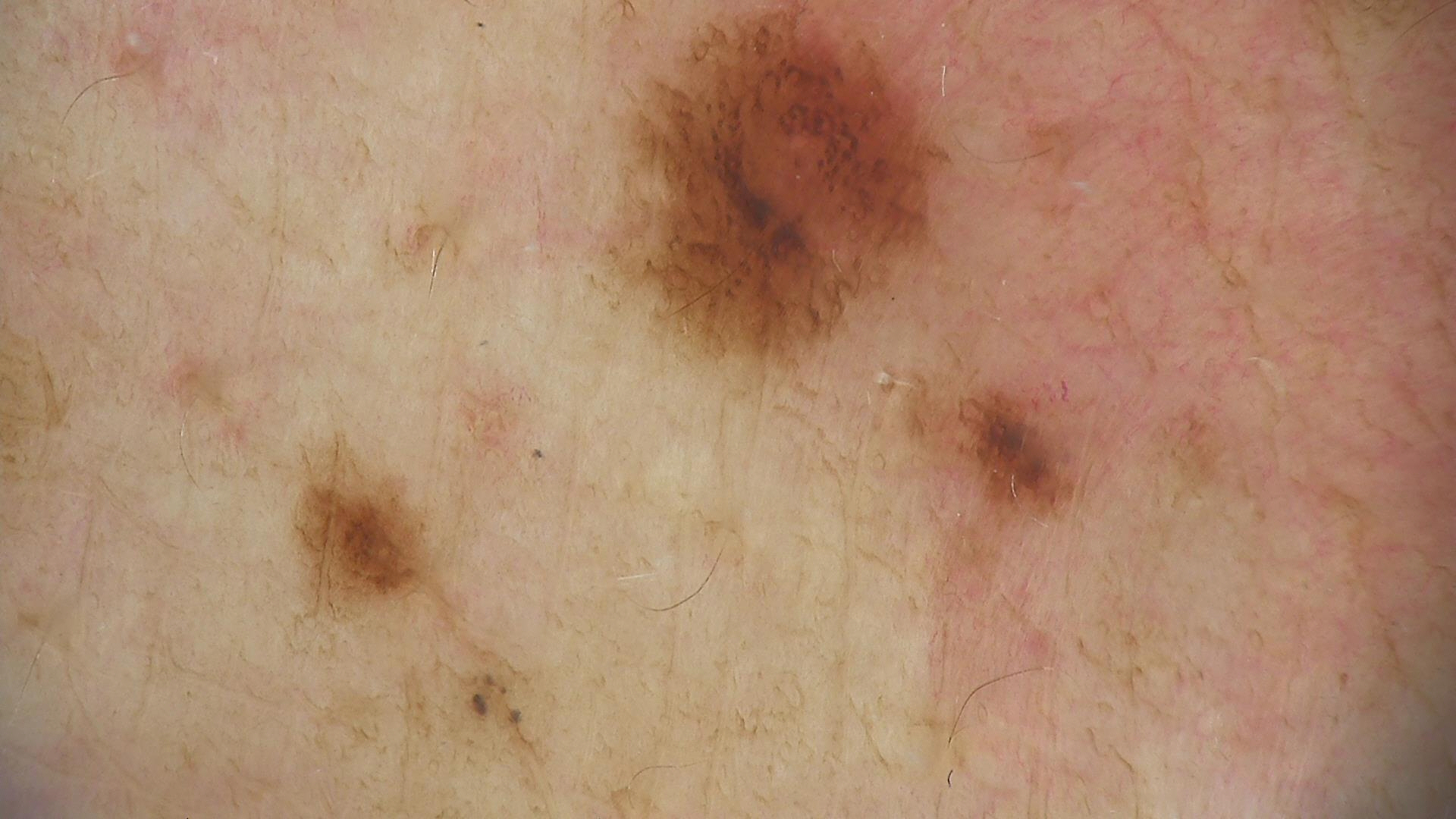A dermatoscopic image of a skin lesion. This is a banal lesion. Labeled as a congenital junctional nevus.